A dermoscopic close-up of a skin lesion. A female subject in their mid-40s:
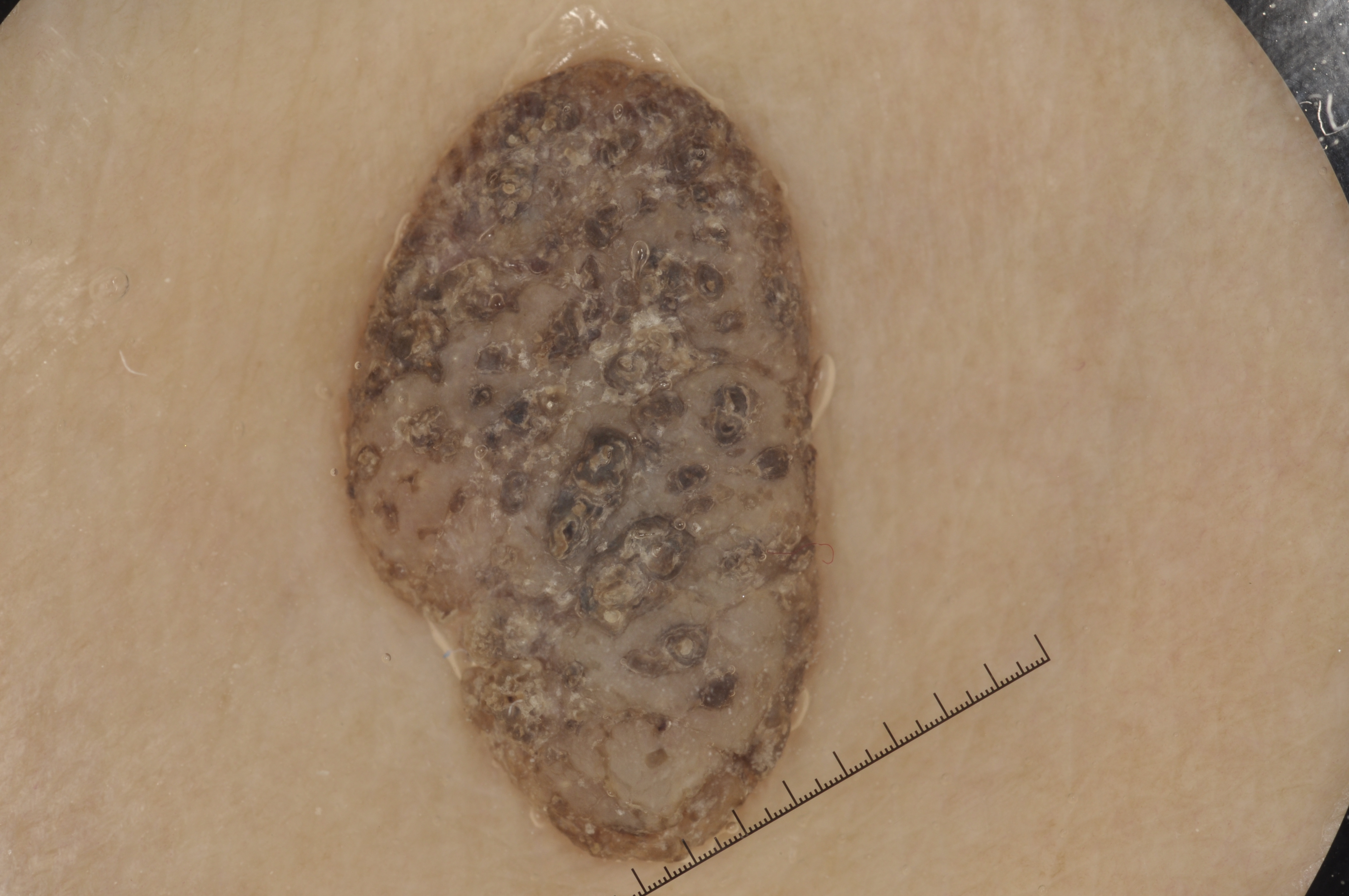Findings: Dermoscopy demonstrates no streaks, negative network, milia-like cysts, or pigment network. With coordinates (x1, y1, x2, y2), the lesion is bounded by (334, 54, 836, 874). A moderately sized lesion. Conclusion: Diagnosed as a seborrheic keratosis, a non-melanocytic (keratinocytic) lesion.